The photo was captured at a distance; the subject is female; located on the leg: 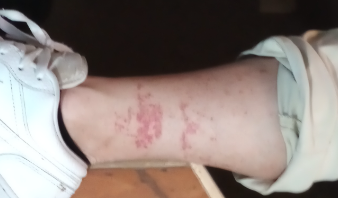Notes:
- texture · flat
- self-categorized as · a rash
- onset · less than one week
- constitutional symptoms · none reported
- reported symptoms · bothersome appearance
- impression · the favored diagnosis is Pigmented purpuric eruption